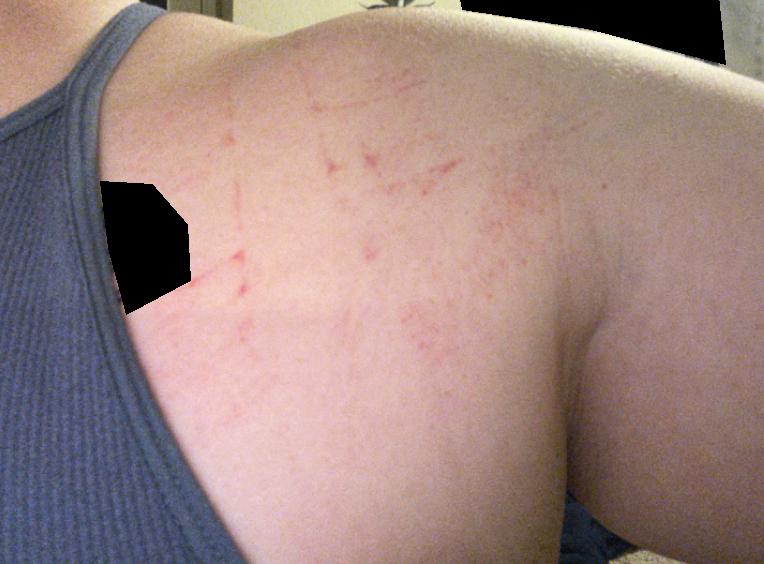{
  "shot_type": "close-up",
  "differential": {
    "tied_lead": [
      "Allergic Contact Dermatitis",
      "Irritant Contact Dermatitis"
    ]
  }
}